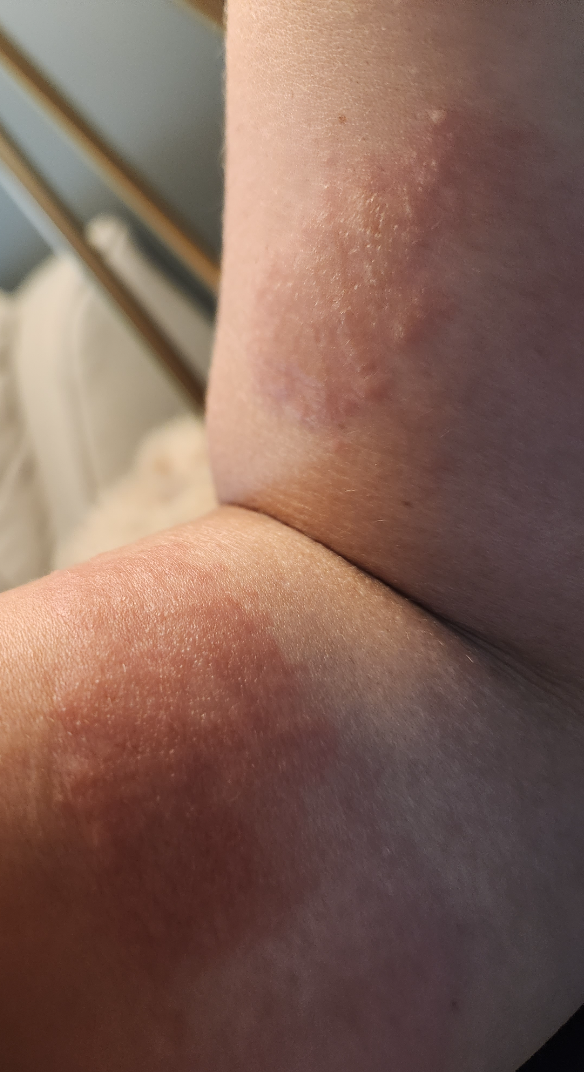Impression: On photographic review by a dermatologist: Photodermatitis (considered); Acute and chronic dermatitis (considered).